A dermoscopy image of a single skin lesion:
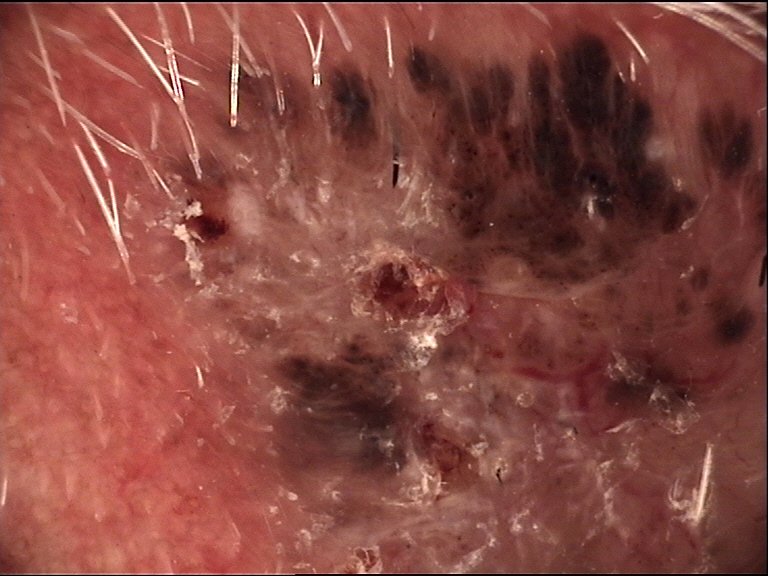Conclusion: The biopsy diagnosis was a basal cell carcinoma.